The contributor is a female aged 40–49; located on the top or side of the foot; a close-up photograph:
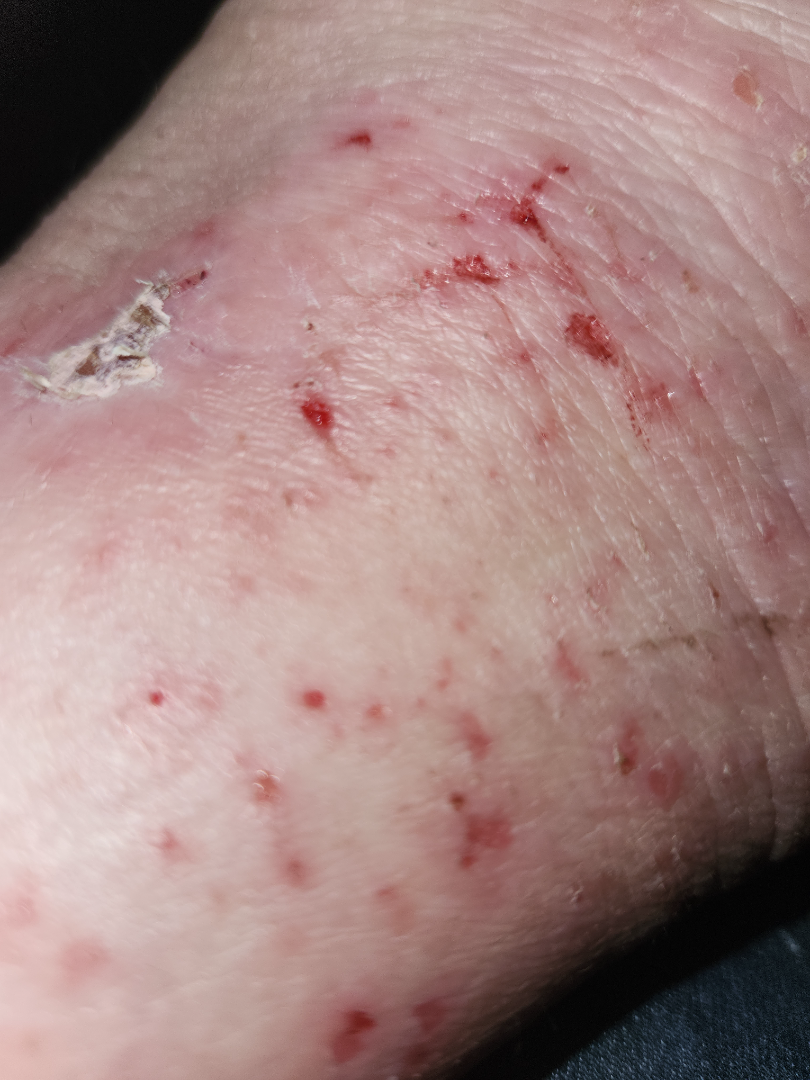| feature | finding |
|---|---|
| assessment | ungradable on photographic review |
| systemic symptoms | none reported |
| texture | rough or flaky |
| onset | one to three months |
| patient's own categorization | a rash |
| skin tone | self-reported FST IV; lay reviewers estimated a MST of 2 |